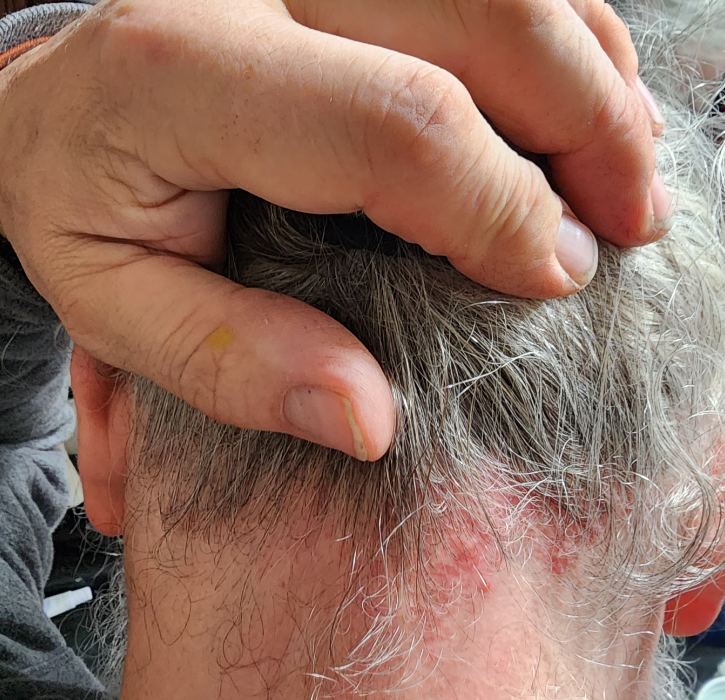Q: Age and sex?
A: male, age 50–59
Q: How does the patient describe it?
A: a rash
Q: Any systemic symptoms?
A: none reported
Q: When did this start?
A: less than one week
Q: Reported symptoms?
A: bothersome appearance, enlargement and itching
Q: How does the lesion feel?
A: raised or bumpy
Q: What is the affected area?
A: head or neck
Q: How was the photo taken?
A: at a distance
Q: What is the dermatologist's impression?
A: most likely Seborrheic Dermatitis; with consideration of Psoriasis